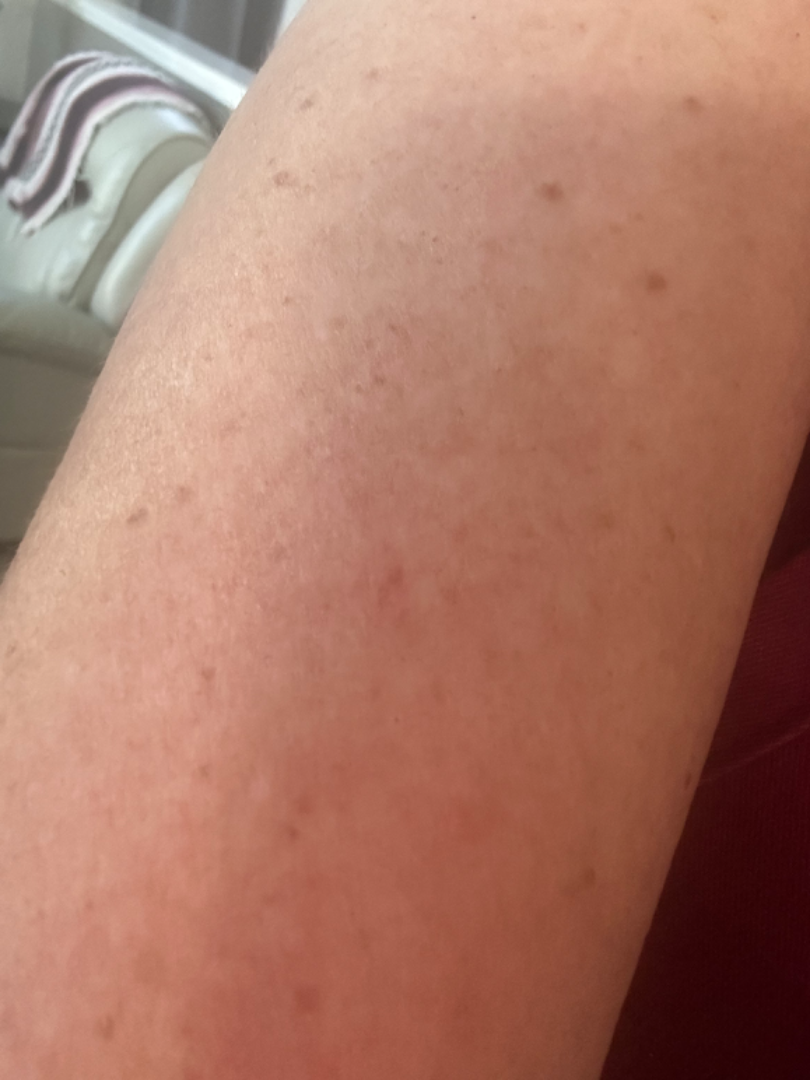assessment = none discernible; anatomic site = arm; view = close-up.